Dermoscopy of a skin lesion:
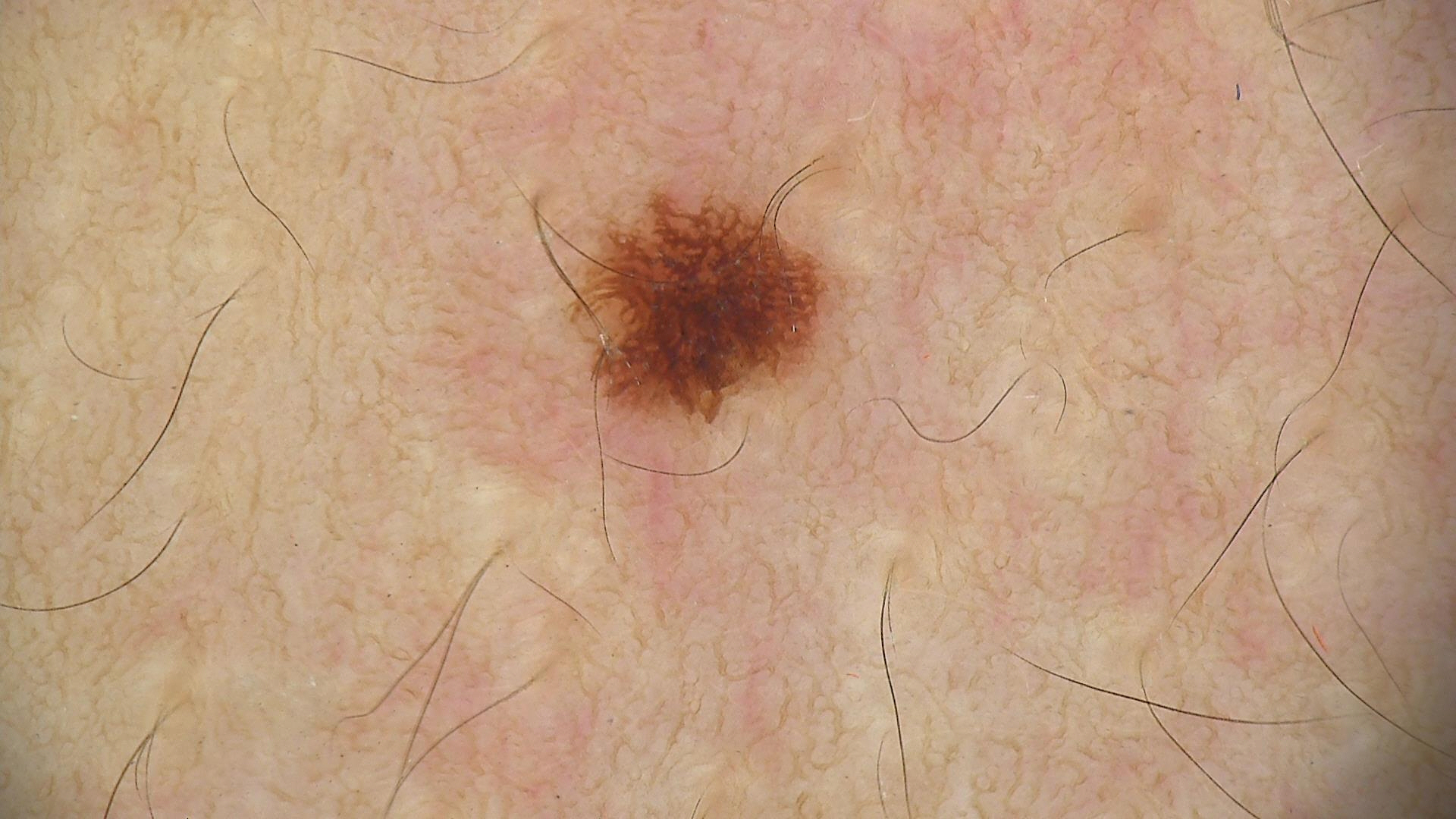diagnostic label = dysplastic junctional nevus (expert consensus).